The subject is male, a close-up photograph.
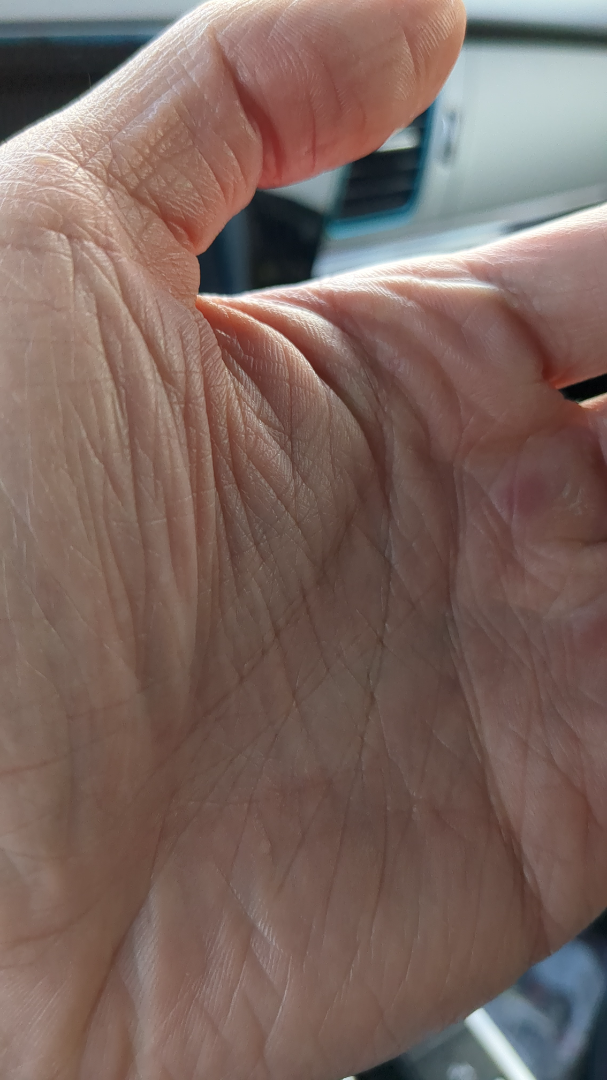The reviewing dermatologist was unable to assign a differential diagnosis from the image.